A dermoscopy image of a single skin lesion:
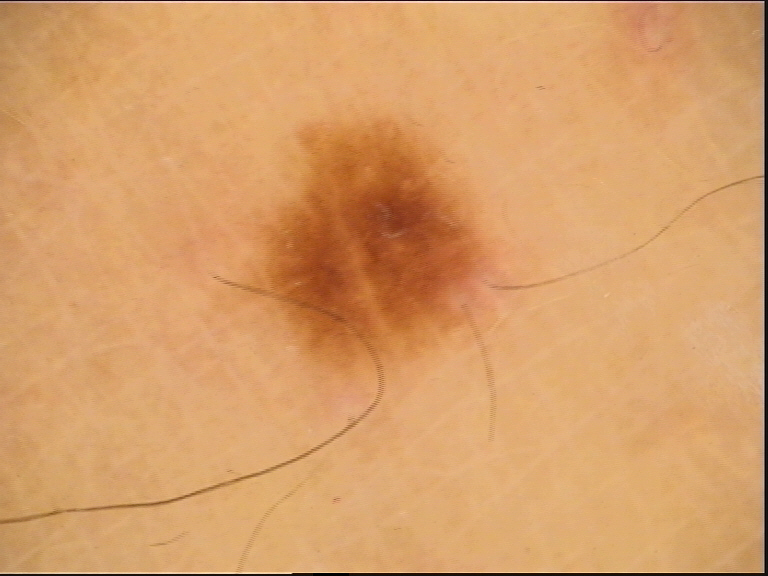Impression:
The diagnostic label was a benign lesion — a dysplastic junctional nevus.